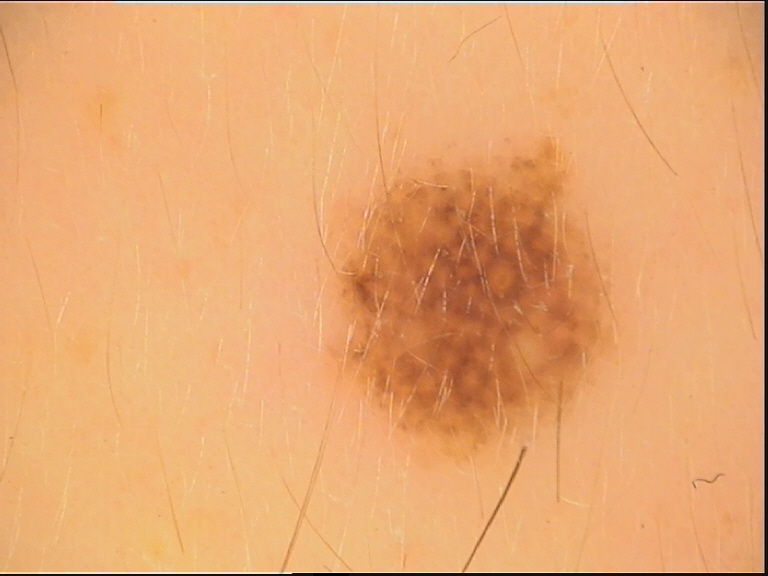Q: What kind of image is this?
A: dermatoscopy
Q: What is the lesion category?
A: compound, banal
Q: What was the diagnostic impression?
A: Miescher nevus (expert consensus)